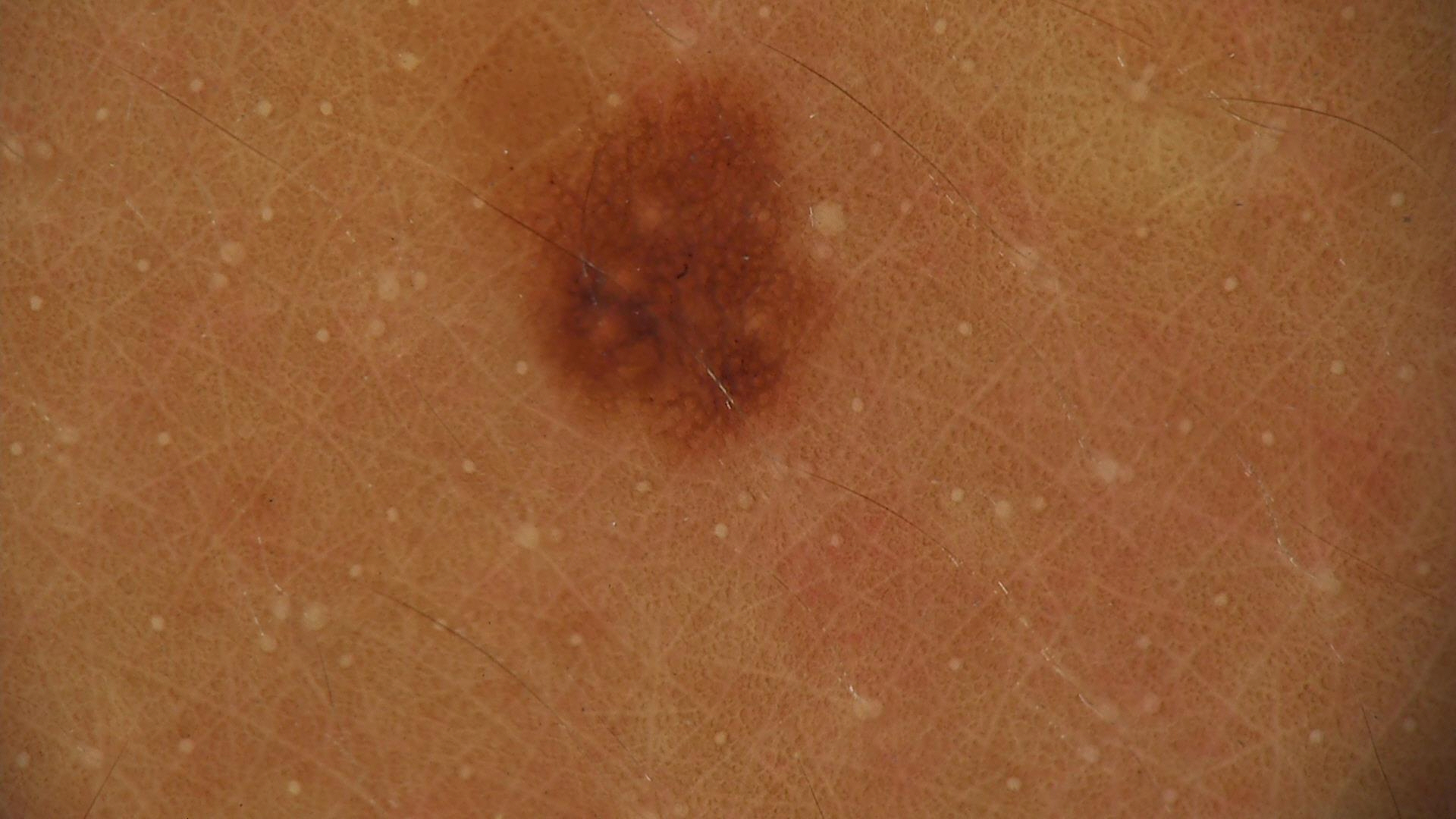Conclusion:
Labeled as a dysplastic junctional nevus.